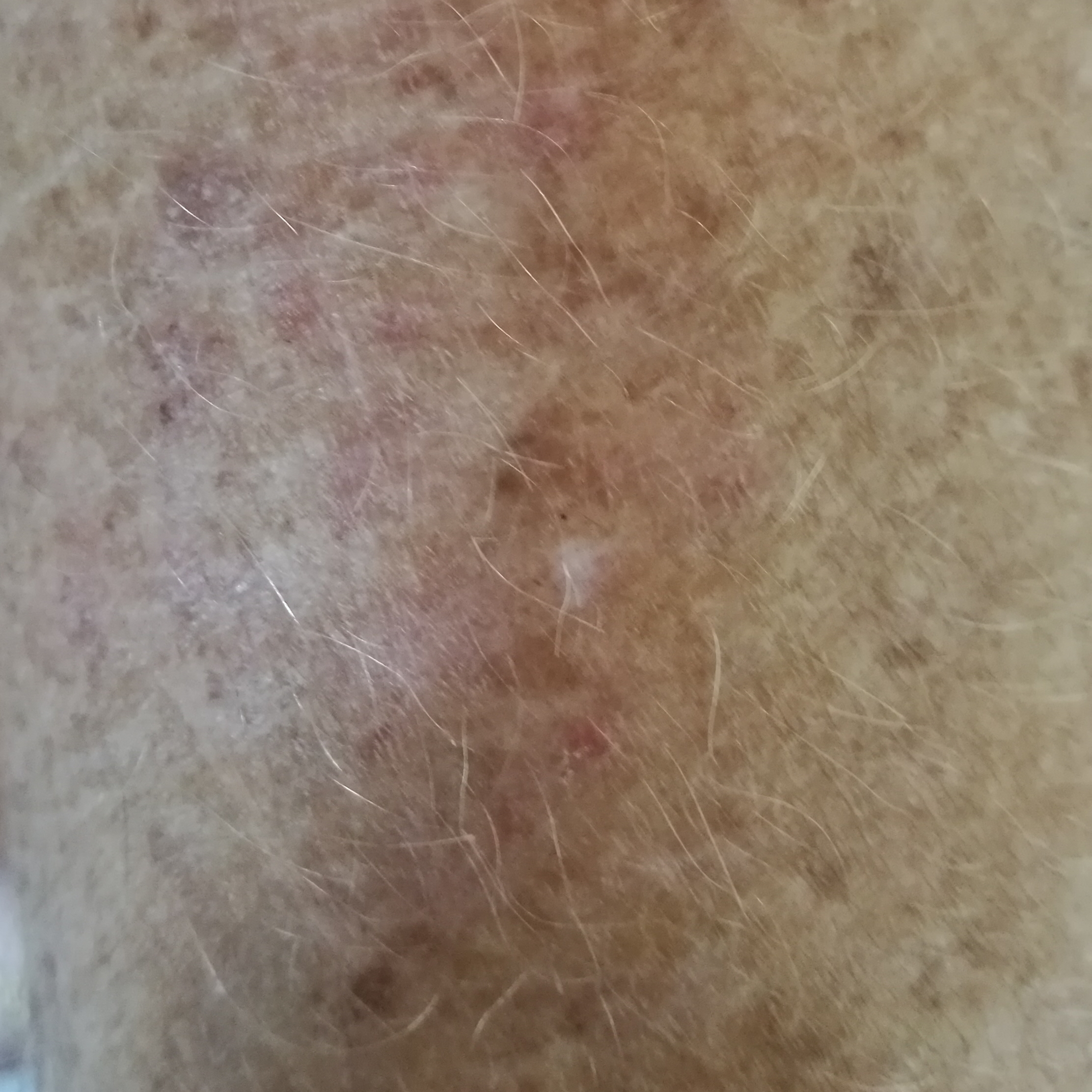modality = clinical photograph; subject = 58 years old; body site = a forearm; reported symptoms = itching / no growth; assessment = actinic keratosis (clinical consensus).